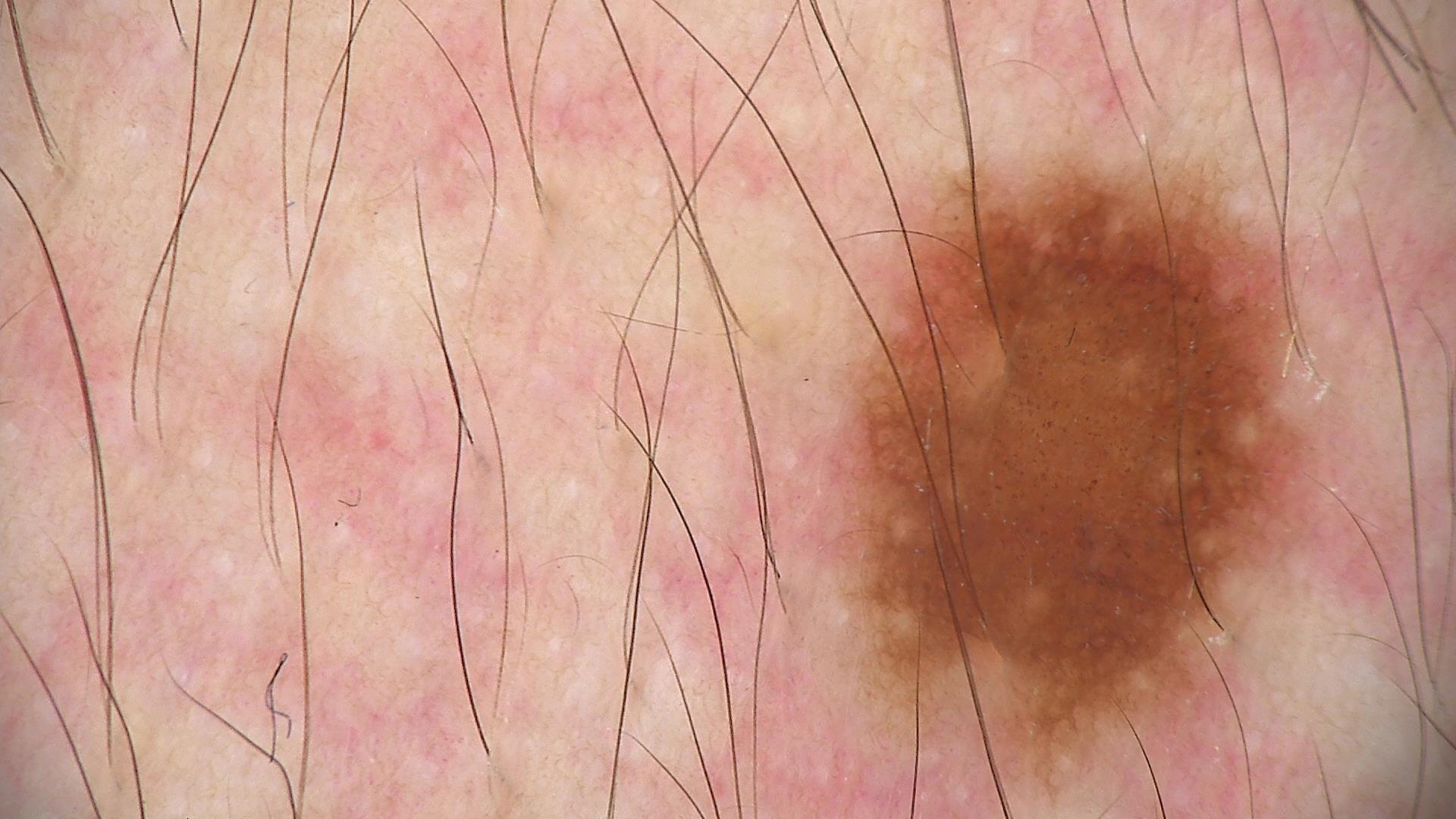– modality — dermatoscopy
– diagnostic label — dysplastic junctional nevus (expert consensus)